This is a close-up image · the arm is involved.
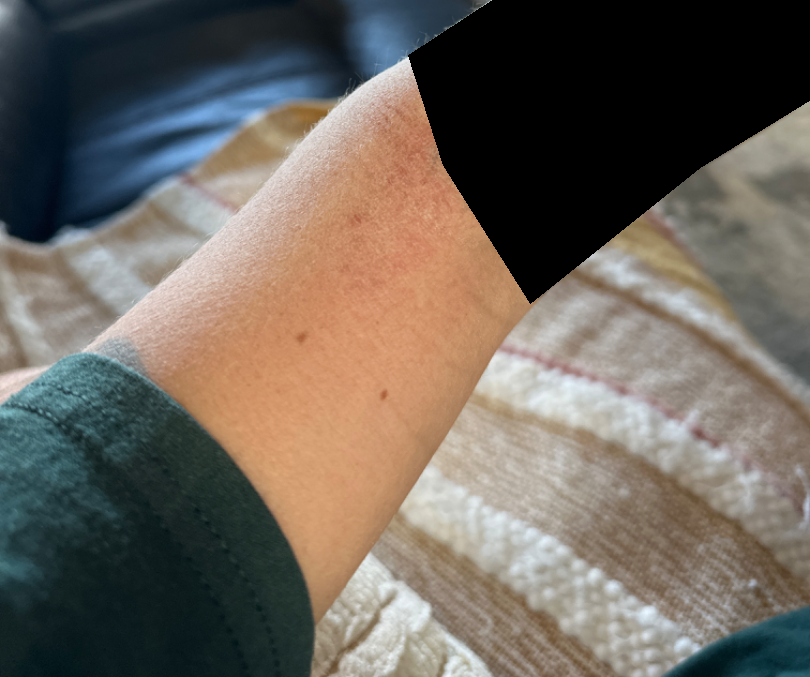The reviewing dermatologist's impression was: most consistent with Eczema.